An image taken at an angle · the lesion involves the leg:
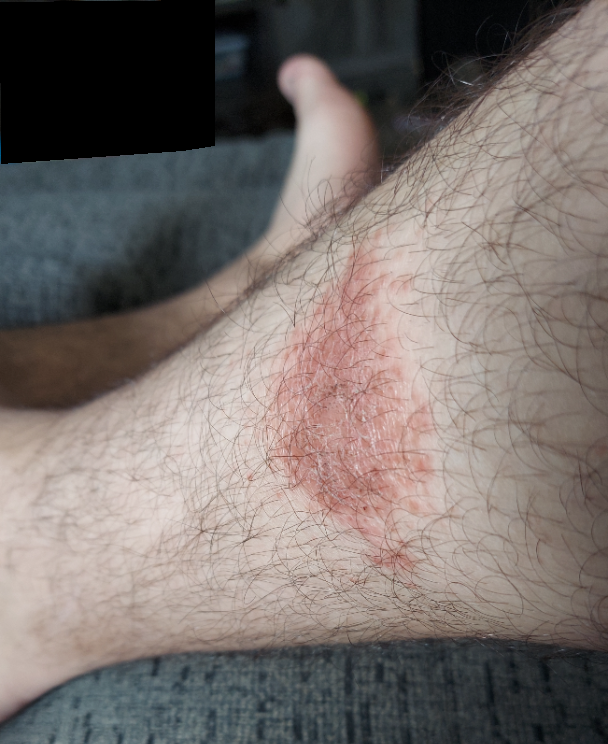history: one to four weeks | texture: rough or flaky | symptoms: enlargement and itching | other reported symptoms: none reported | assessment: Eczema (primary).